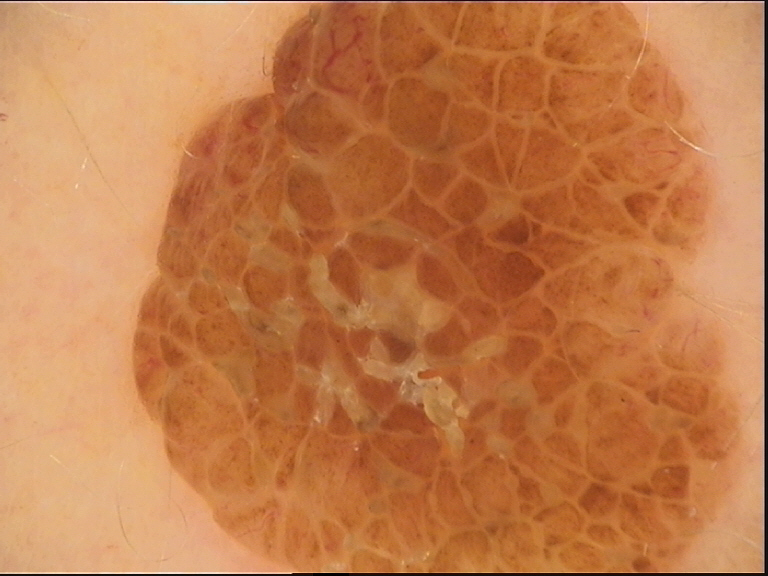Impression:
Diagnosed as a banal lesion — a compound nevus.